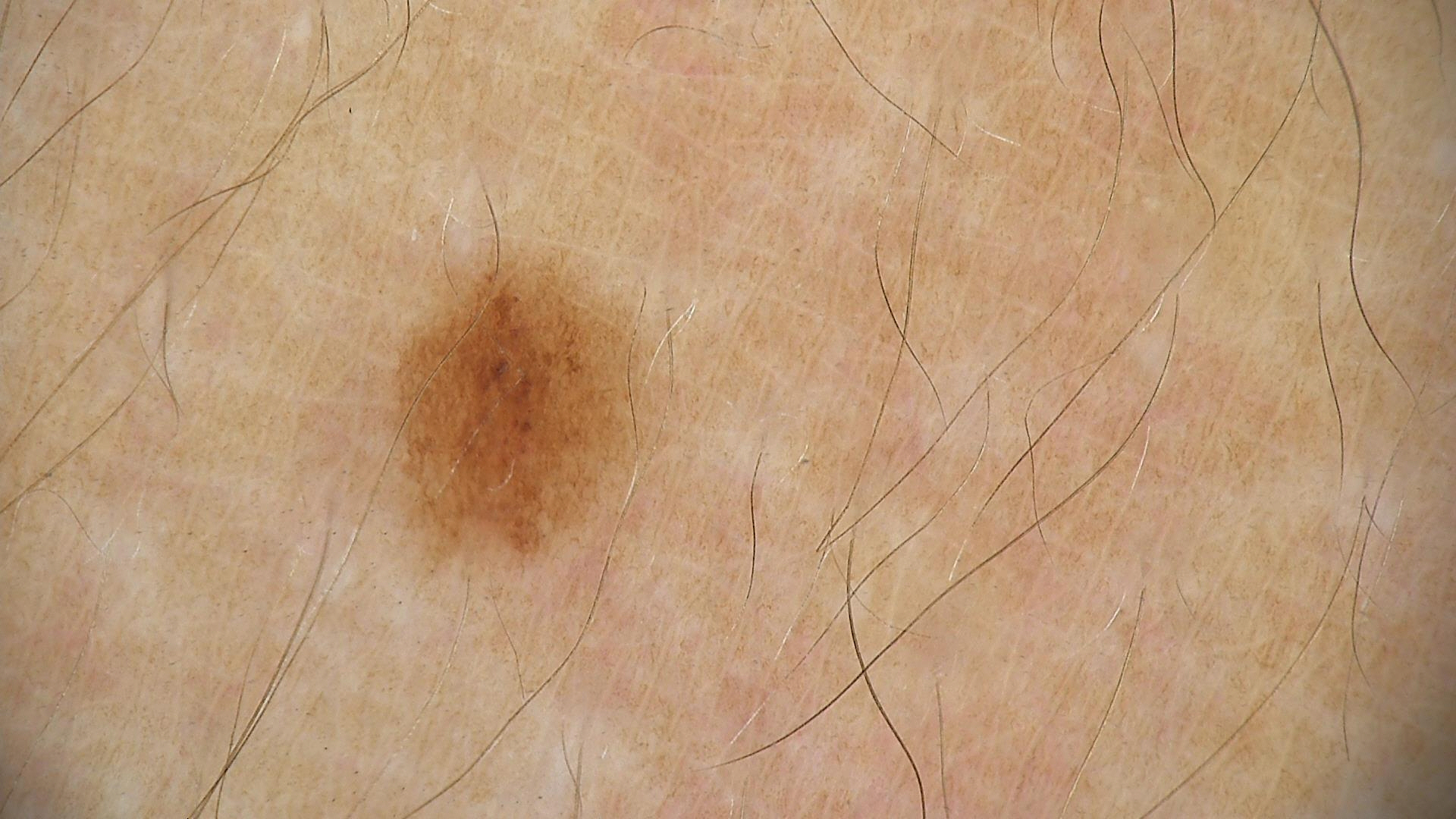imaging = dermatoscopy; diagnosis = dysplastic junctional nevus (expert consensus).